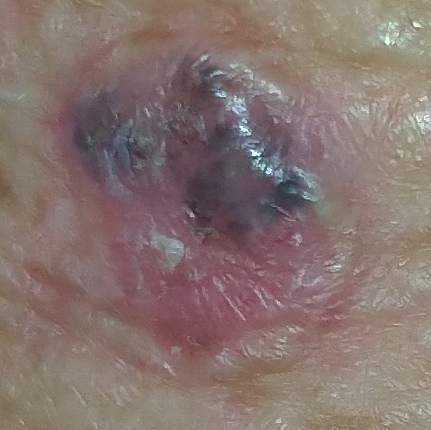By history, prior malignancy (patient or family) and prior skin cancer (patient or family). A clinical photo of a skin lesion taken with a smartphone. A female subject in their 60s. The patient is skin type III. The lesion measures 12 × 11 mm. Per patient report, the lesion itches and is elevated. Biopsy-confirmed as a basal cell carcinoma.